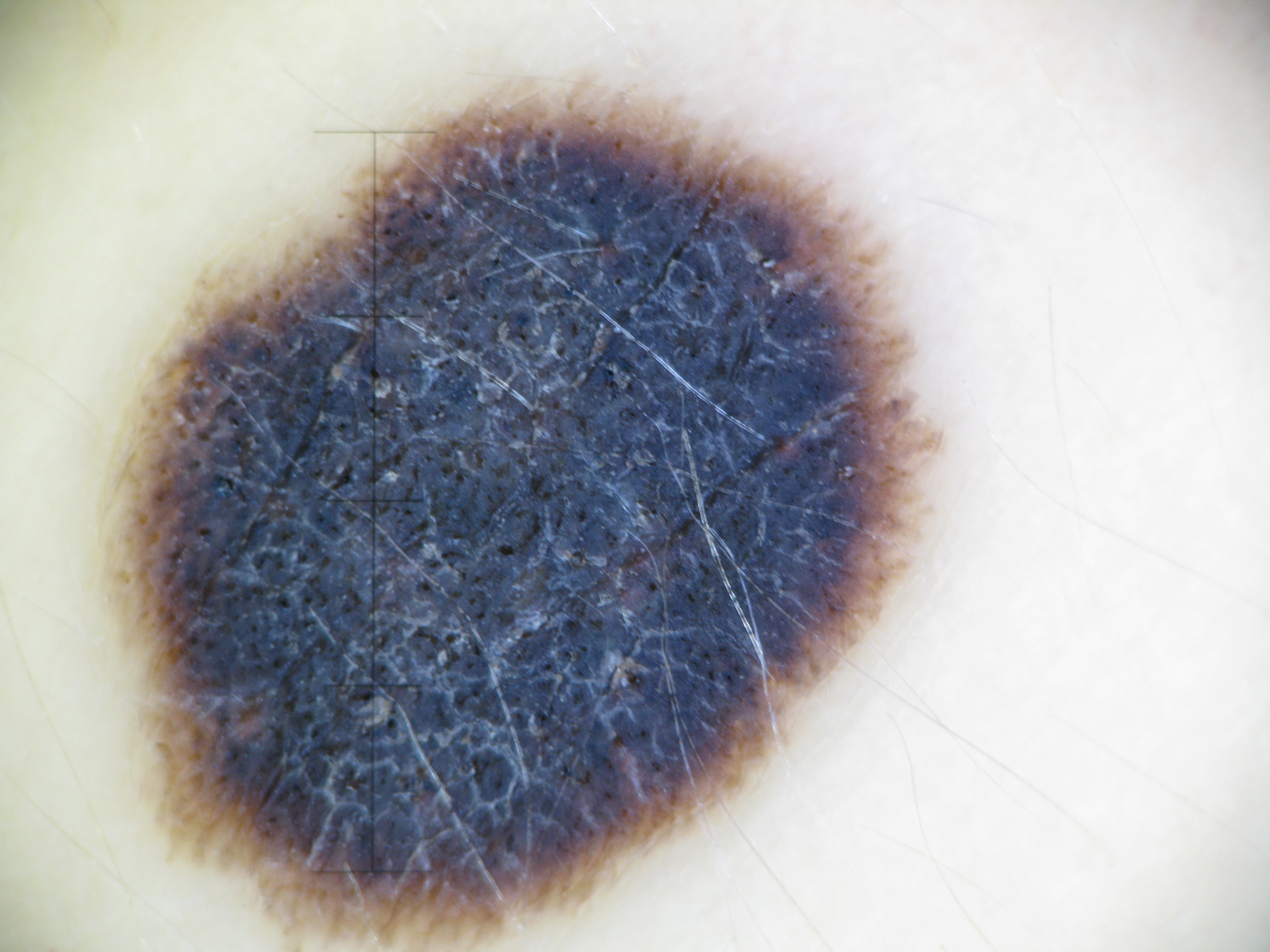A dermoscopic photograph of a skin lesion. This is a junctional, dysplastic lesion. Diagnosed as a benign lesion — a Spitz/Reed nevus.